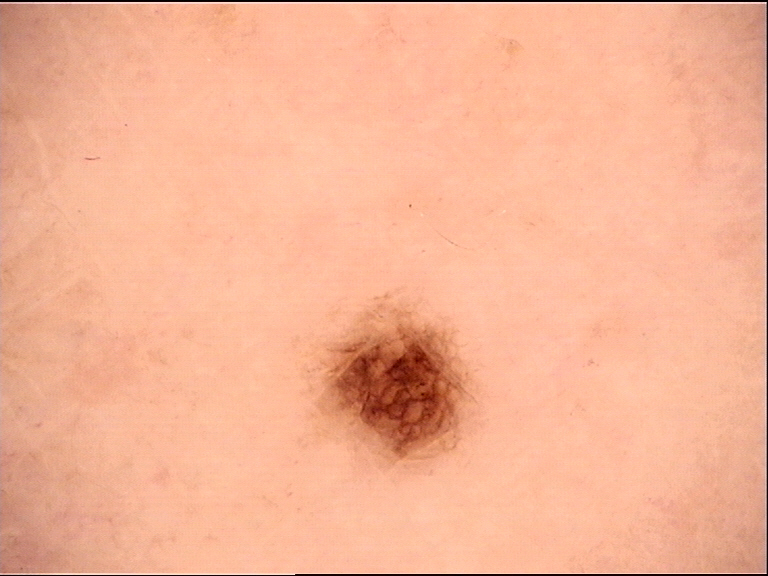| feature | finding |
|---|---|
| imaging | dermoscopy |
| label | dysplastic junctional nevus (expert consensus) |